The patient also reports fatigue. The patient considered this a rash. Located on the arm. A close-up photograph. The lesion is described as raised or bumpy. The lesion is associated with itching and enlargement. Female patient, age 50–59:
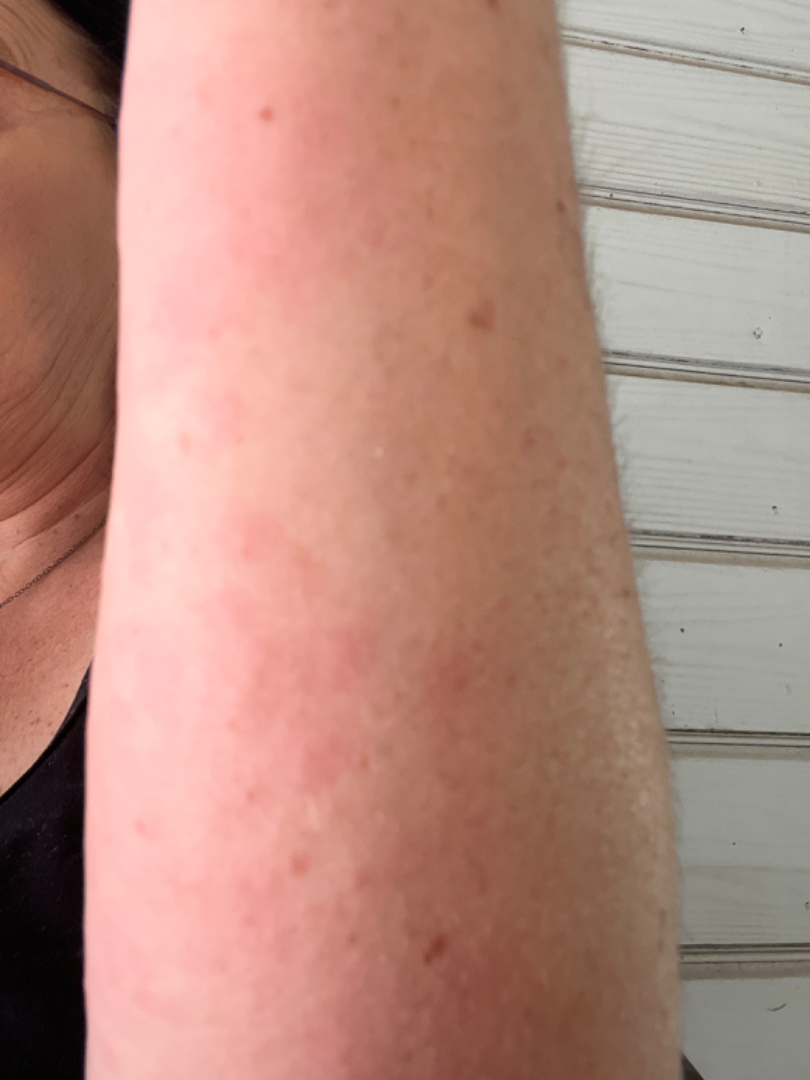Findings:
* differential diagnosis: Urticaria, Eczema and Allergic Contact Dermatitis were each considered, in no particular order